This is a close-up image, the patient is a female aged 60–69, the arm is involved.
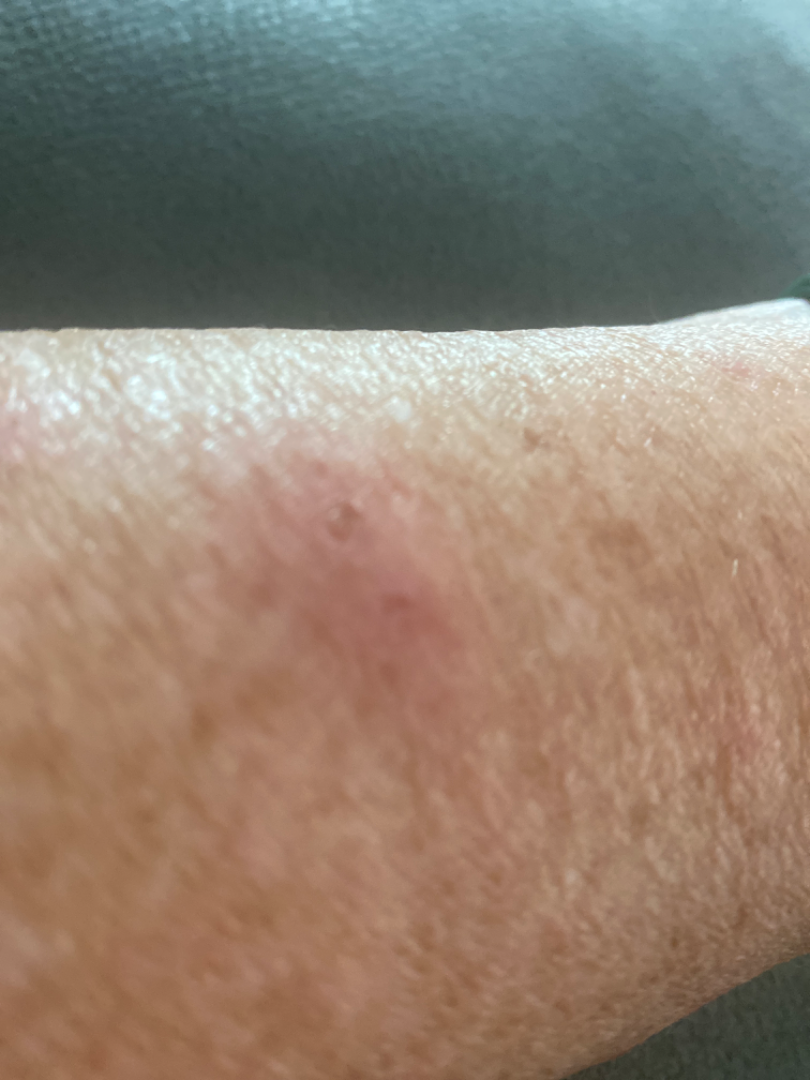Findings: Diagnostic features were not clearly distinguishable in this photograph.